A dermoscopic image of a skin lesion:
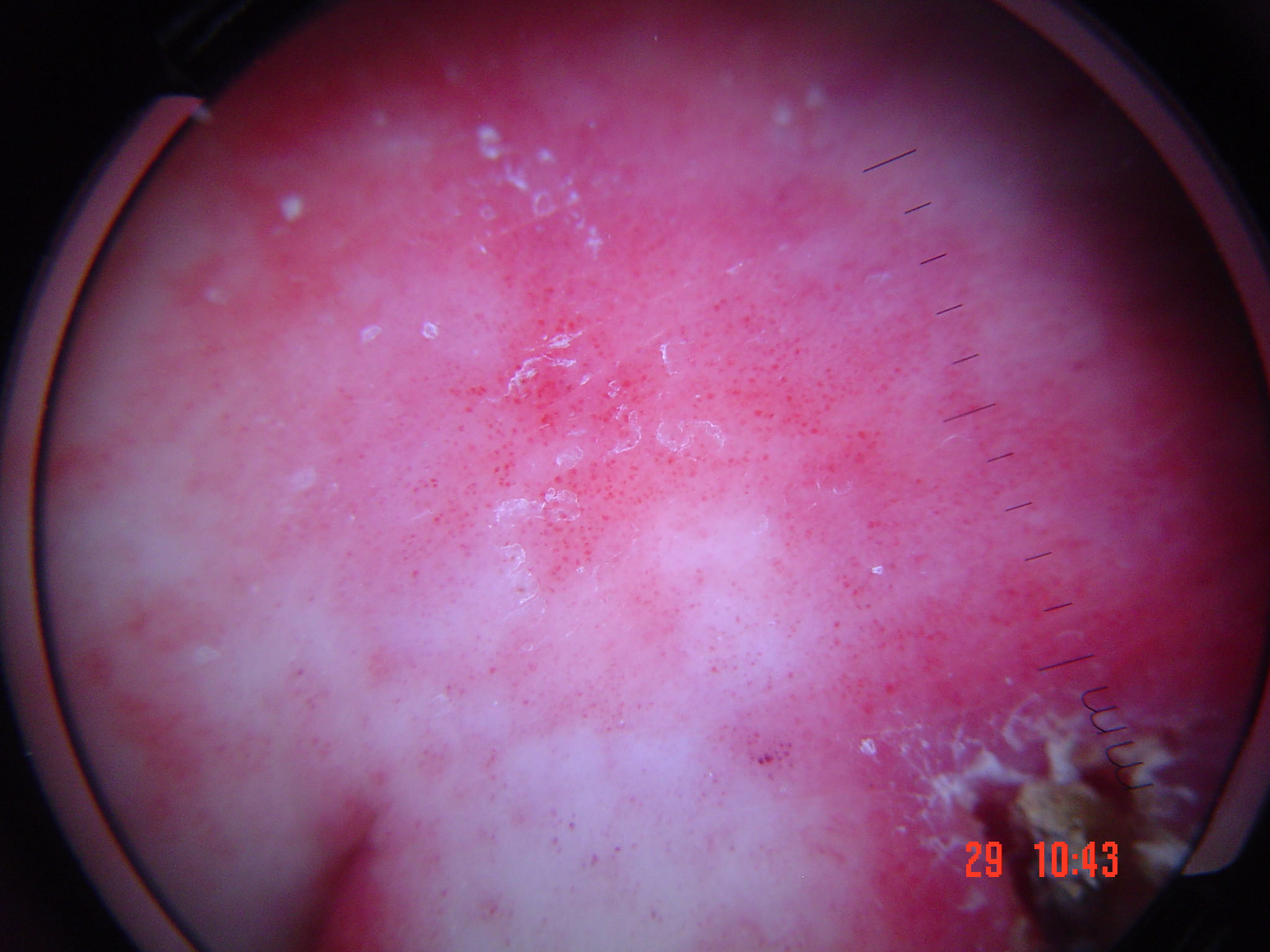The morphology is that of a vascular lesion. Diagnosed as a hemangioma.